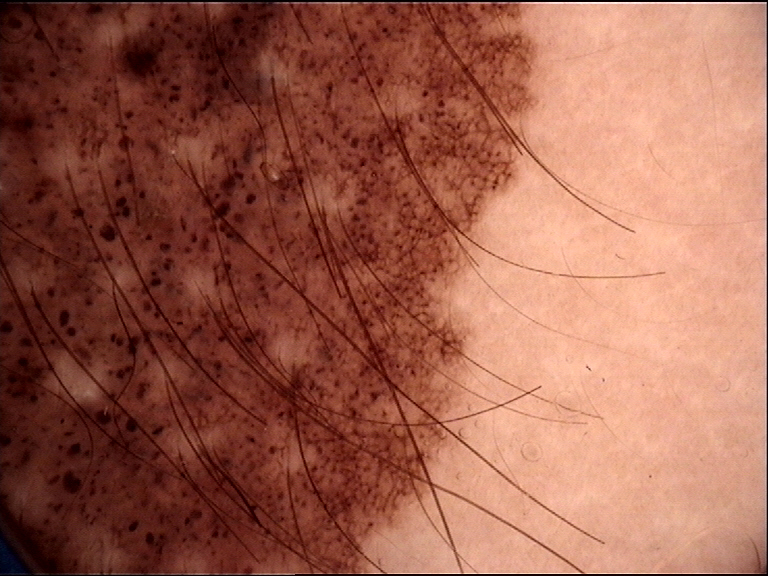diagnosis:
  name: congenital compound nevus
  code: ccb
  malignancy: benign
  super_class: melanocytic
  confirmation: expert consensus